A skin lesion imaged with a dermatoscope.
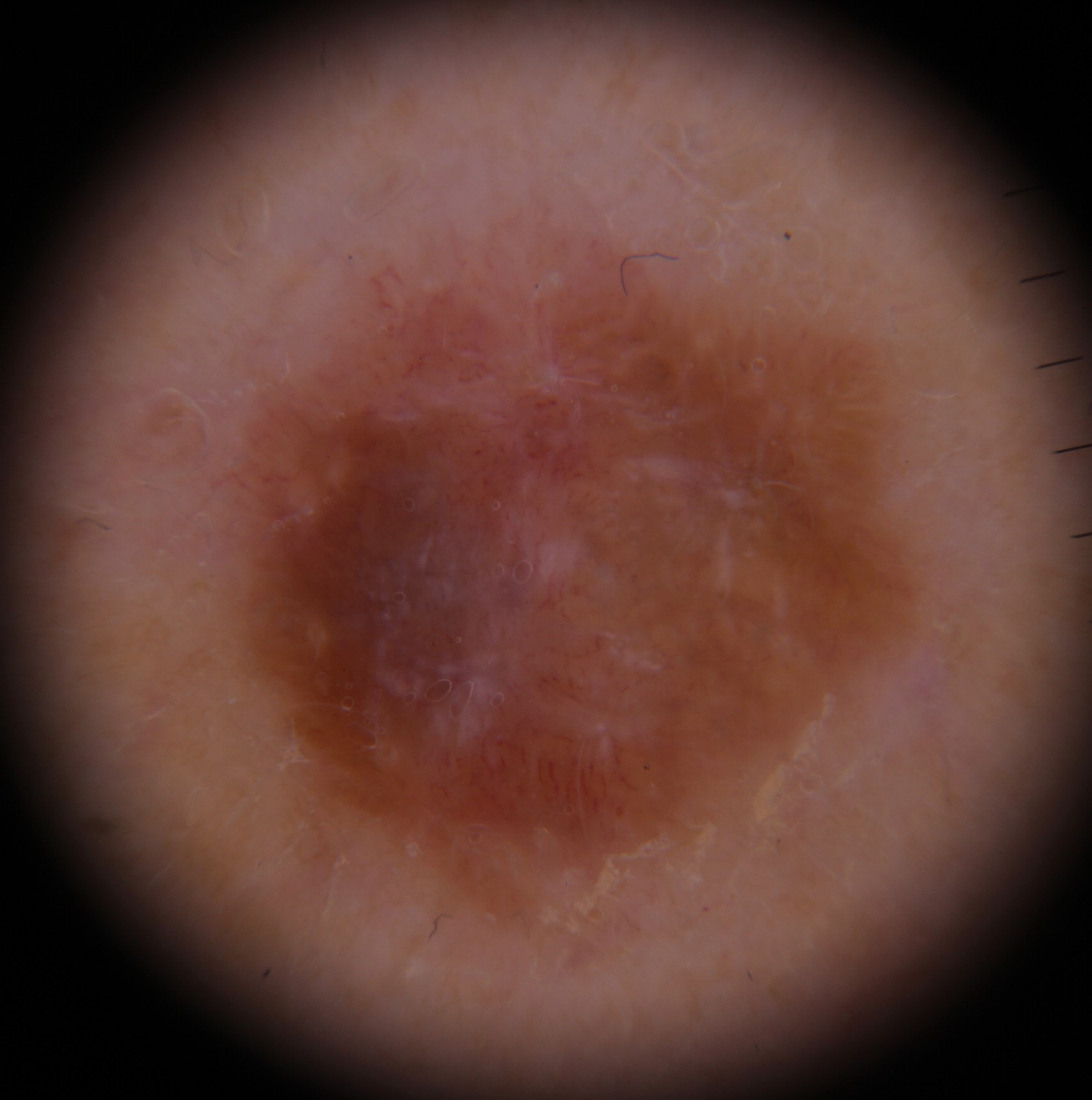class=melanoma (biopsy-proven).